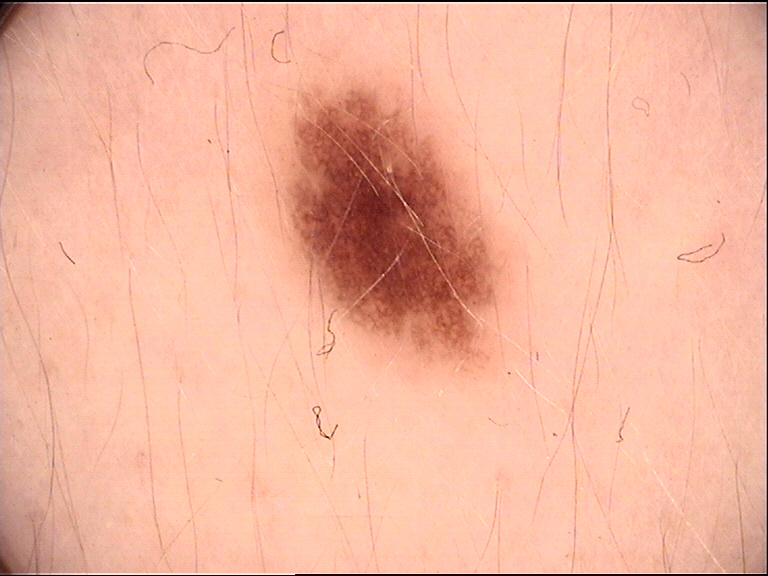This is a banal lesion. The diagnosis was a junctional nevus.